This is a close-up image · skin tone: Fitzpatrick skin type V; human graders estimated Monk skin tone scale 3 or 5 (two reviewer pools disagreed):
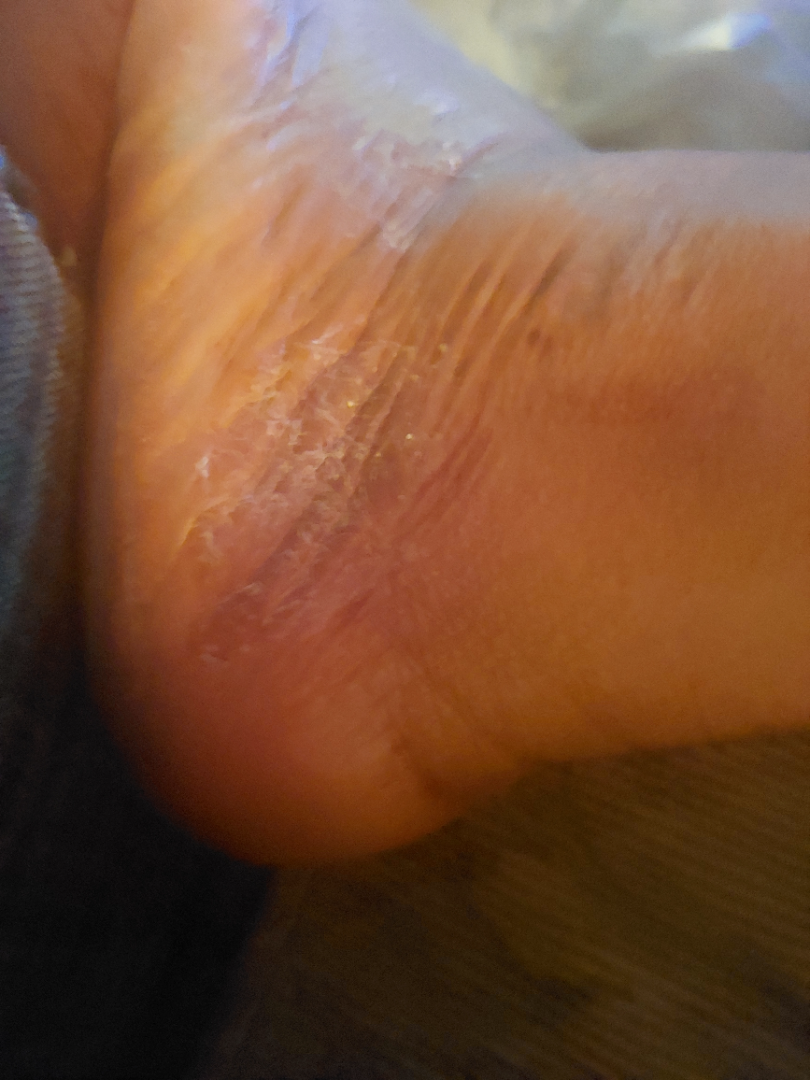| key | value |
|---|---|
| clinical impression | Psoriasis (possible); Eczema (possible); Tinea (remote) |